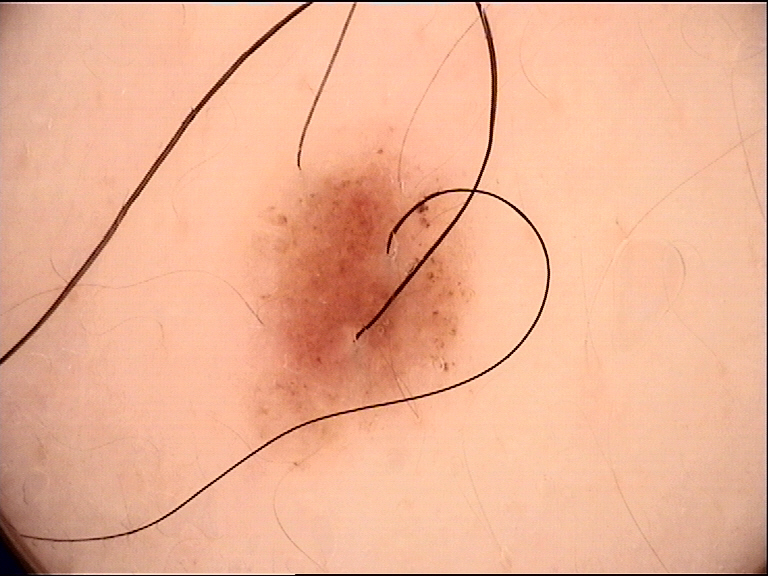Dermoscopy of a skin lesion. Consistent with a benign lesion — a dysplastic junctional nevus.